This is a close-up image. The lesion involves the front of the torso, leg and head or neck:
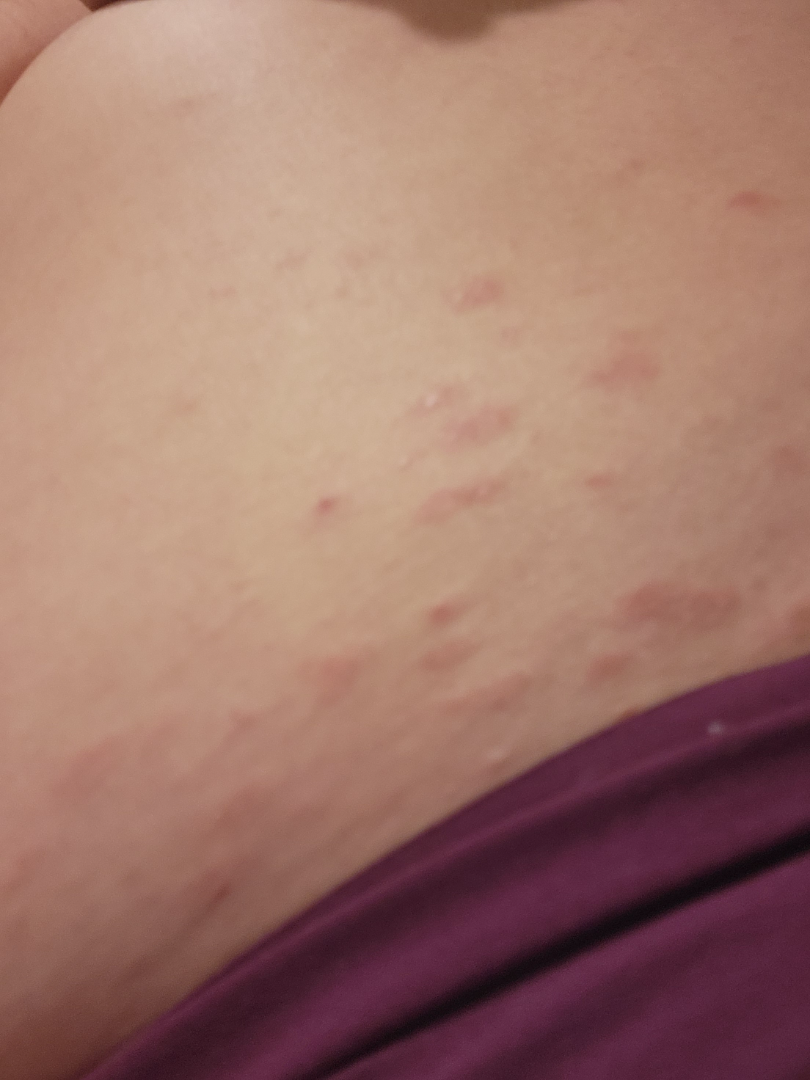diagnostic considerations=Pityriasis rosea (54%); Psoriasis (23%); Eczema (23%).